The patient is 60–69, female. Close-up view — 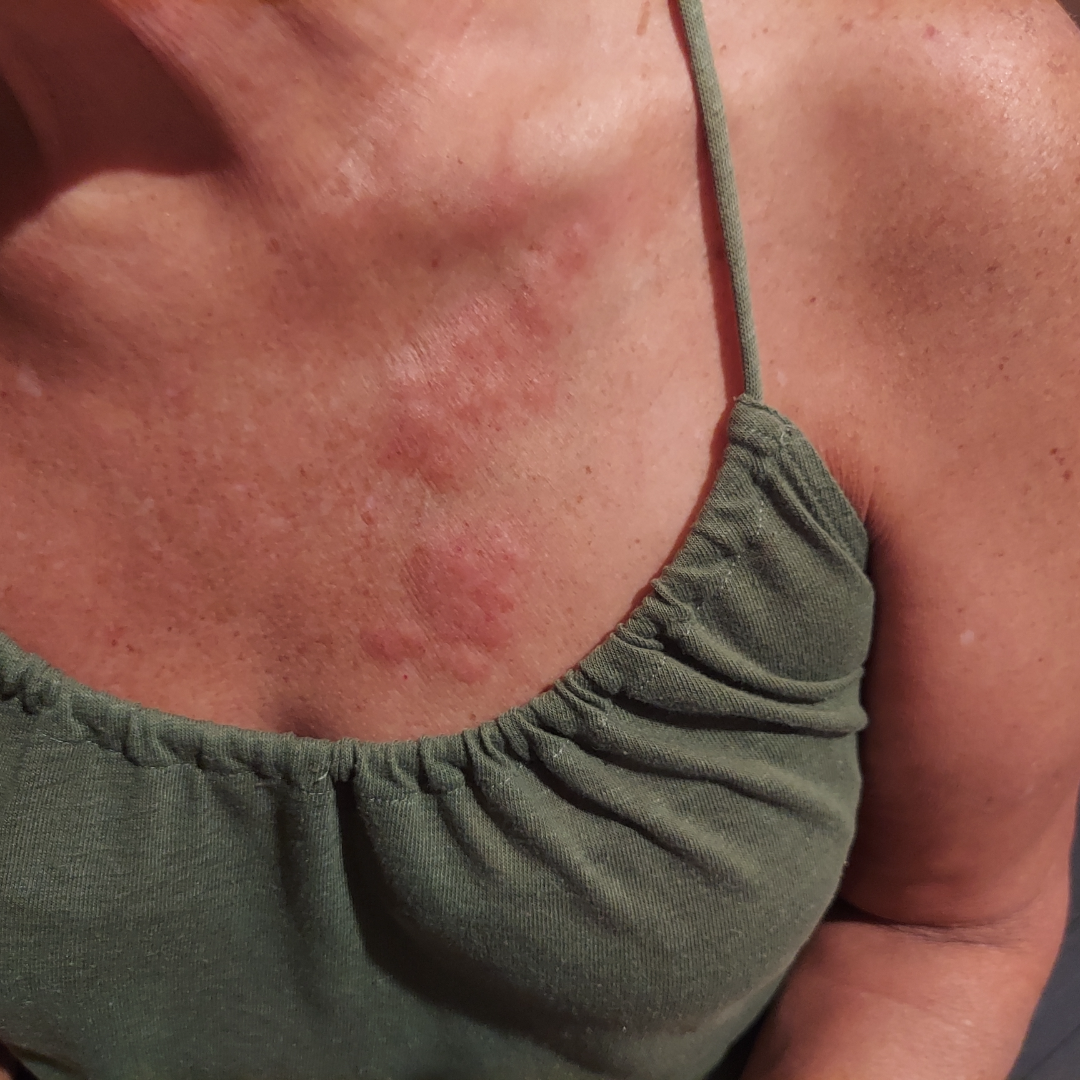Background:
The condition has been present for one to four weeks. The patient indicates enlargement, bothersome appearance and itching. The patient indicates the lesion is raised or bumpy. Self-categorized by the patient as a rash.
Findings:
A single dermatologist reviewed the case: Cutaneous lupus, Insect Bite and Allergic Contact Dermatitis were each considered, in no particular order.